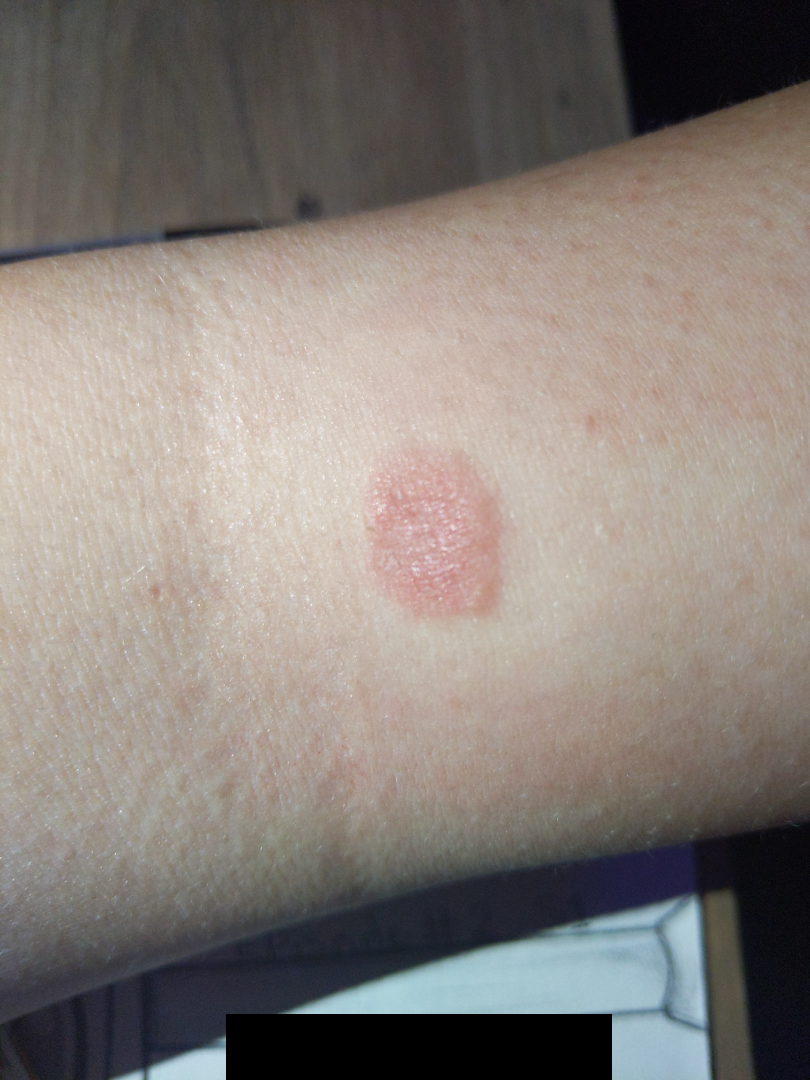History:
The patient considered this a rash. Skin tone: Fitzpatrick II. The affected area is the arm. The condition has been present for less than one week. Close-up view. Female subject, age 18–29. No constitutional symptoms were reported. The lesion is associated with itching and enlargement. The contributor reports the lesion is fluid-filled and raised or bumpy.
Impression:
Most consistent with Eczema; also raised was Insect Bite; less likely is Allergic Contact Dermatitis; a more distant consideration is Pityriasis rosea.